A dermoscopic close-up of a skin lesion — 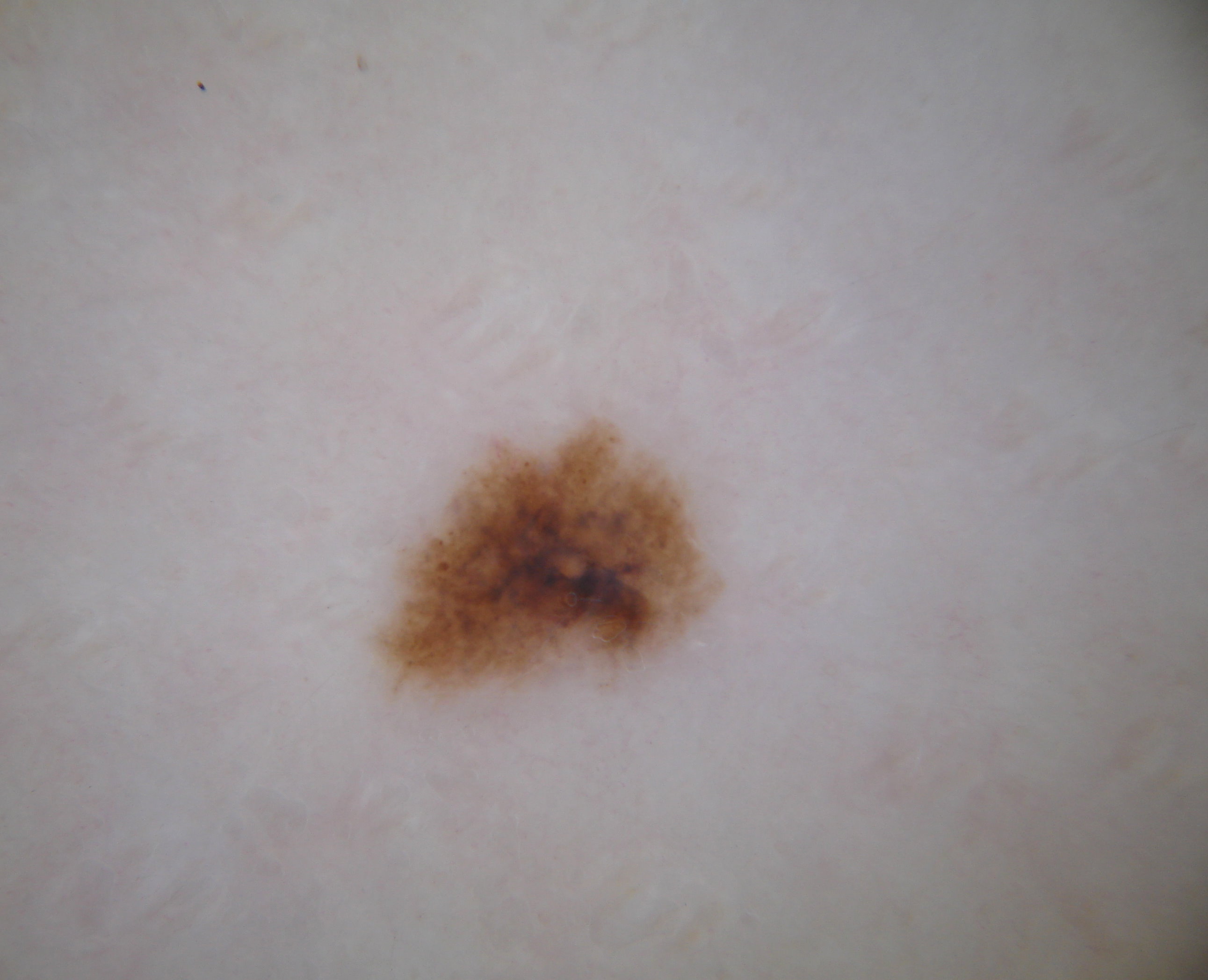Findings: With coordinates (x1, y1, x2, y2), the lesion spans <bbox>363, 414, 726, 733</bbox>. The lesion occupies roughly 7% of the field. On dermoscopy, the lesion shows no negative network, streaks, globules, pigment network, or milia-like cysts. Conclusion: Diagnosed as a melanocytic nevus, a benign lesion.